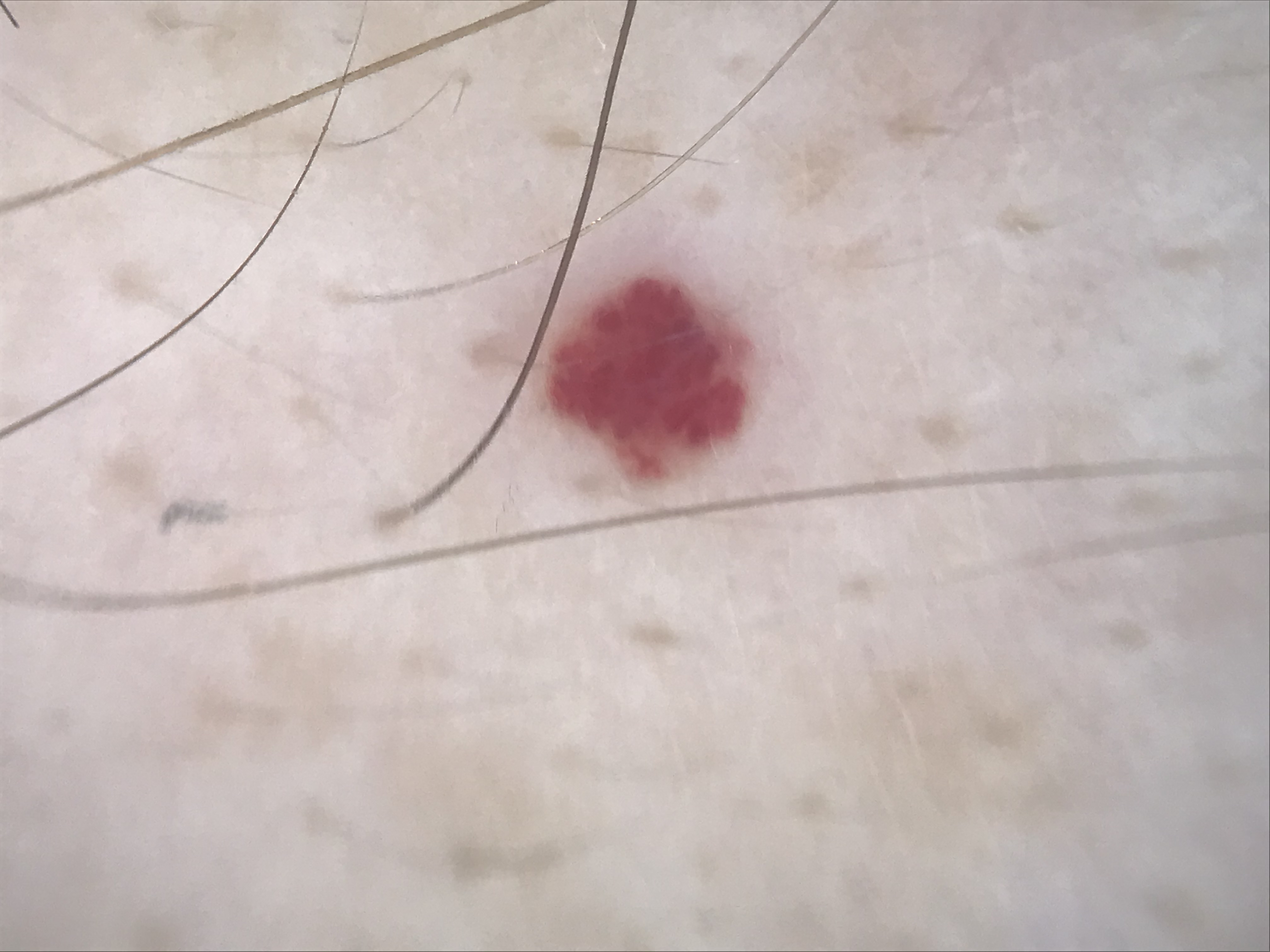  image: dermoscopy
  diagnosis:
    name: hemangioma
    code: ha
    malignancy: benign
    super_class: non-melanocytic
    confirmation: expert consensus